A dermoscopy image of a single skin lesion:
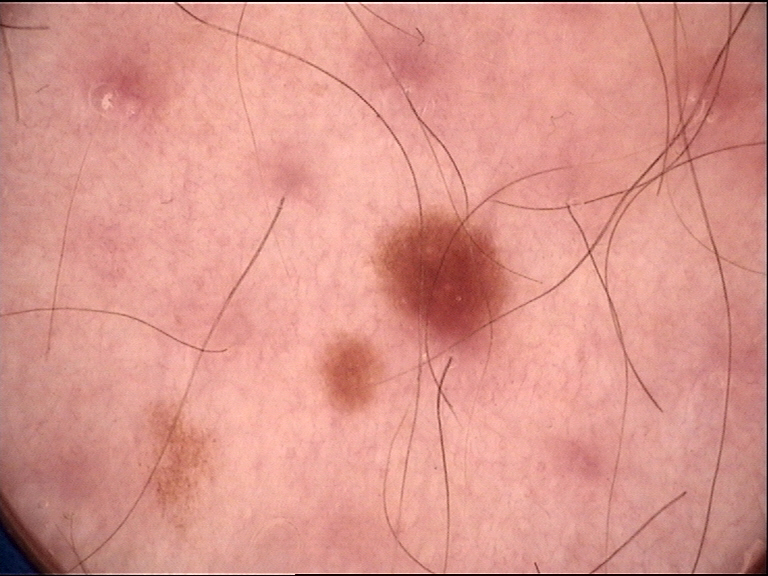Case:
– class — dysplastic junctional nevus (expert consensus)